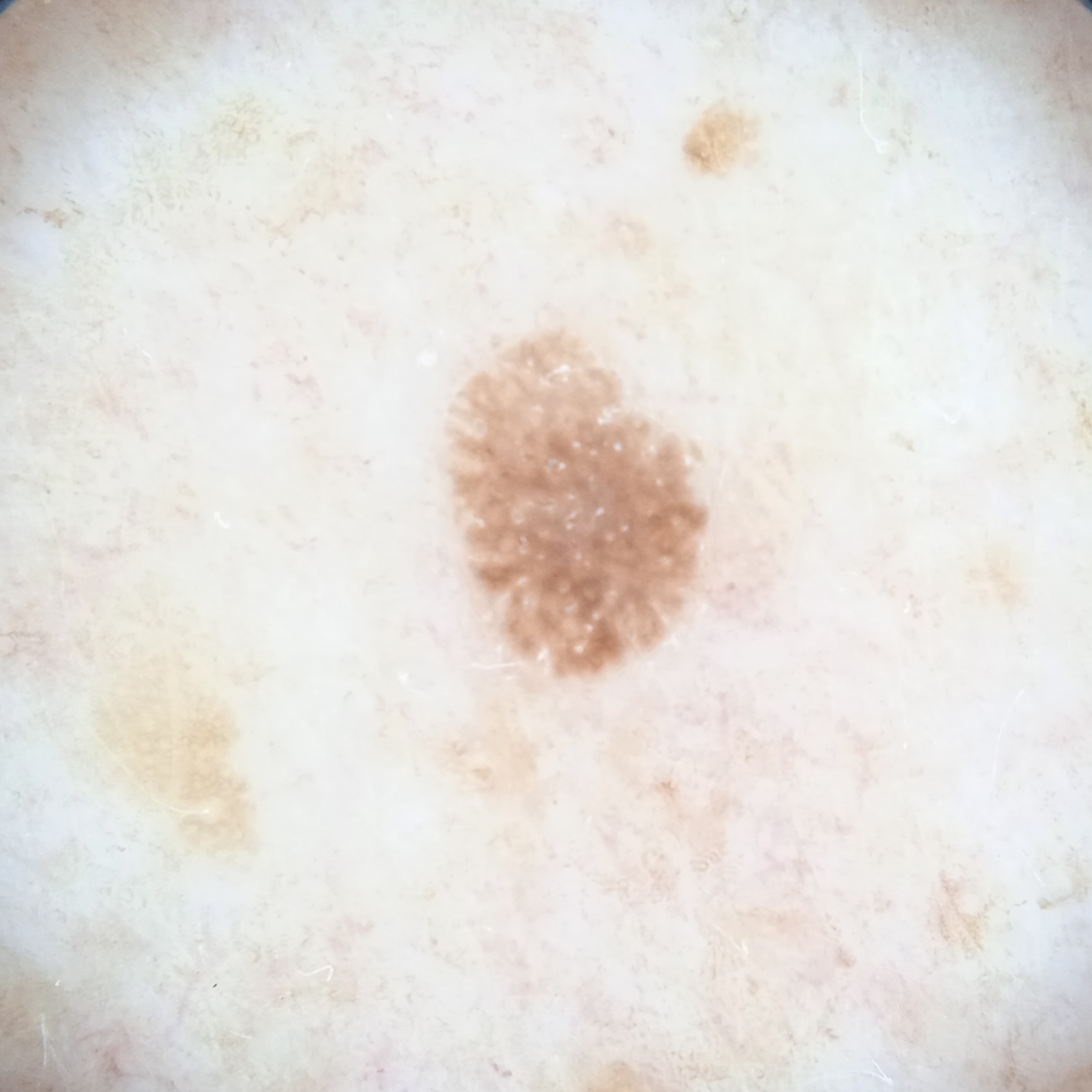{
  "mole_burden": "few melanocytic nevi overall",
  "patient": {
    "age": 62,
    "sex": "male"
  },
  "referral": "research study (no referral diagnosis)",
  "sun_reaction": "skin reddens with sun exposure",
  "image": "dermoscopic image",
  "lesion_location": "the back",
  "lesion_size": {
    "diameter_mm": 4.3
  },
  "diagnosis": {
    "name": "seborrheic keratosis",
    "malignancy": "benign"
  }
}